A dermoscopic photograph of a skin lesion.
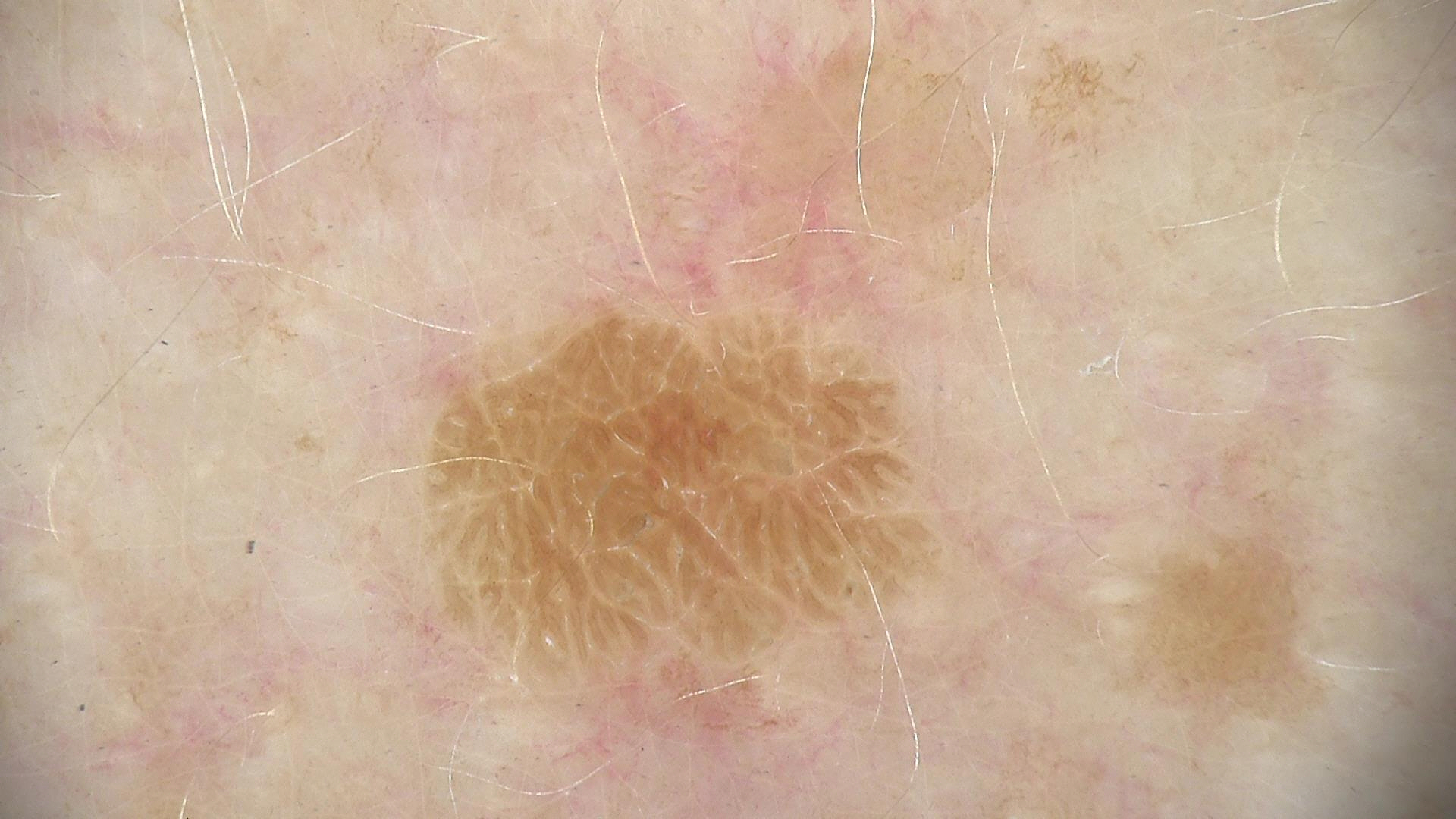| key | value |
|---|---|
| diagnostic label | seborrheic keratosis (expert consensus) |